A clinical close-up photograph of a skin lesion. Skin type II. The chart records pesticide exposure, prior malignancy (patient or family), and no prior skin cancer (patient or family): 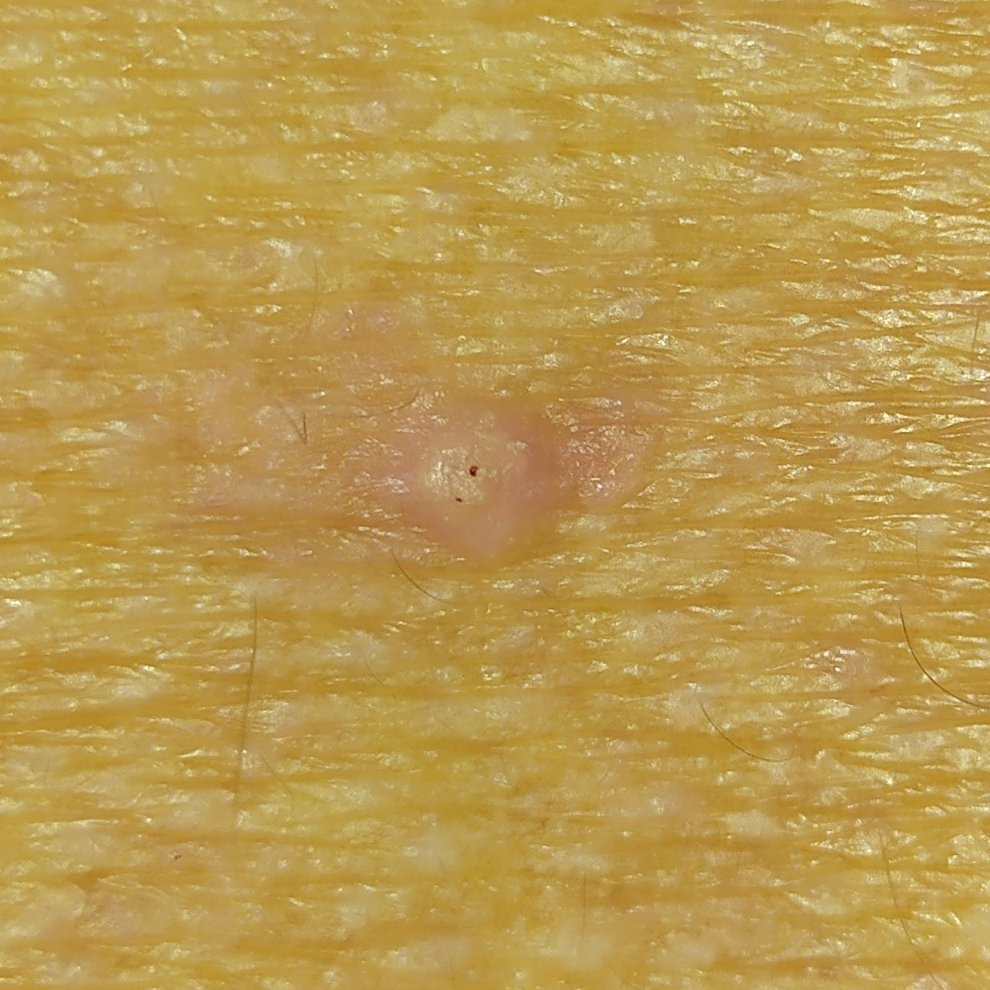The lesion is located on the back.
The lesion measures 4 × 4 mm.
Per patient report, the lesion is elevated.
Biopsy-confirmed as an actinic keratosis.